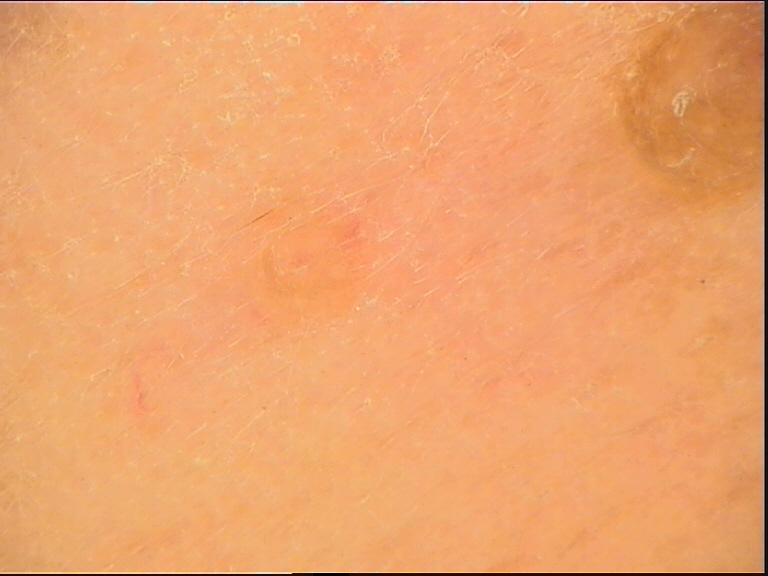assessment = seborrheic keratosis (expert consensus).